Female patient, age 50–59; the affected area is the front of the torso; an image taken at a distance: 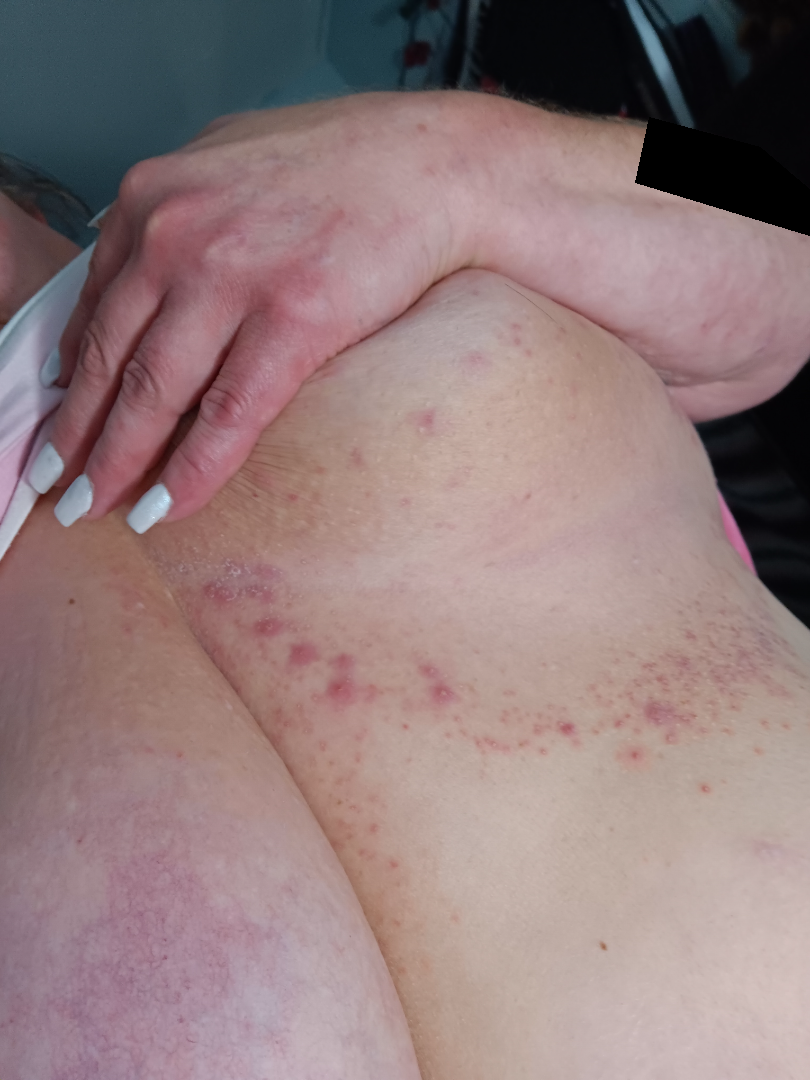On remote dermatologist review: Folliculitis (0.41); Insect Bite (0.41); Localized skin infection (0.18).